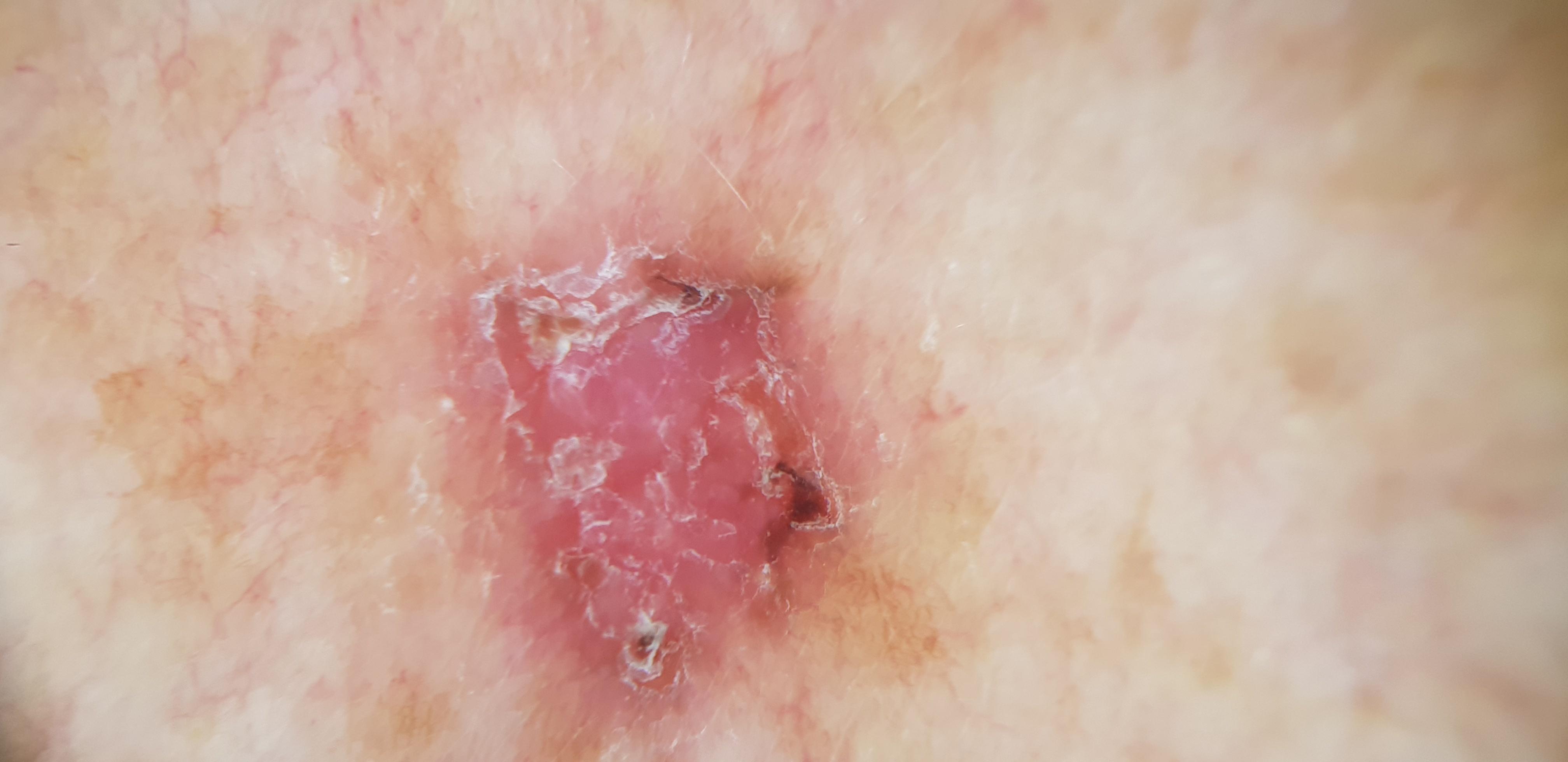<lesion>
<diagnosis>
<name>Basal cell carcinoma</name>
<malignancy>malignant</malignancy>
<confirmation>histopathology</confirmation>
<lineage>adnexal</lineage>
</diagnosis>
</lesion>